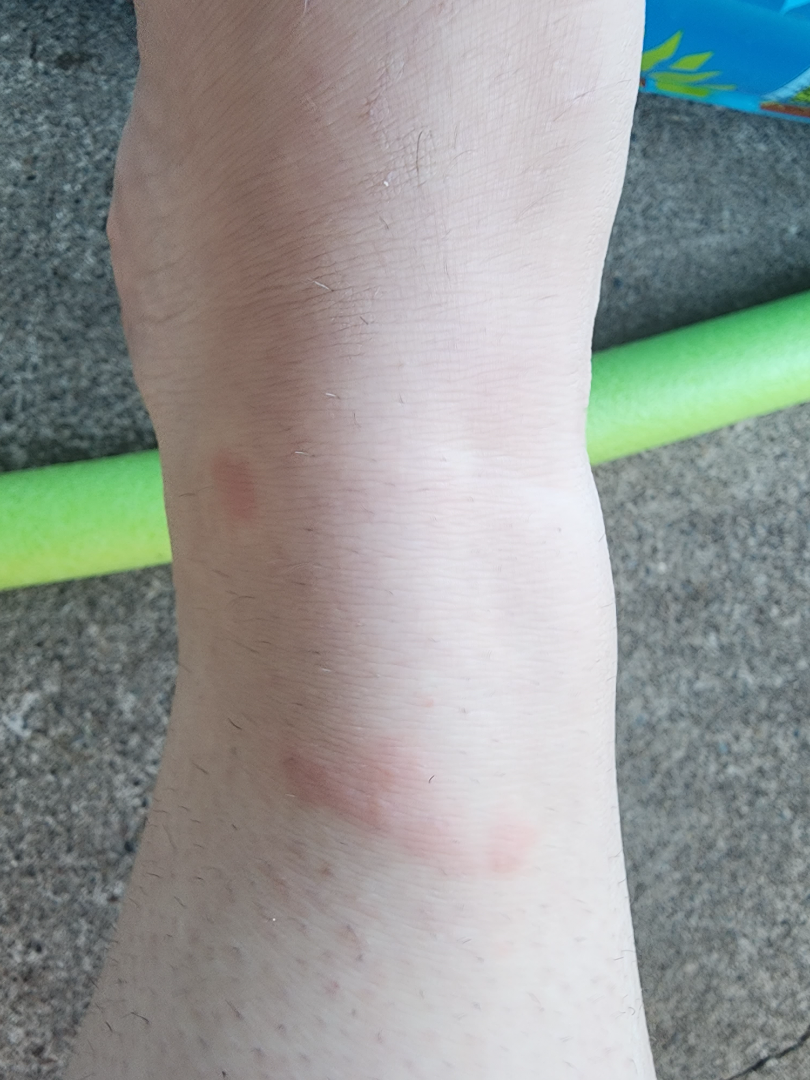Review: The reviewing dermatologist was unable to assign a differential diagnosis from the image. Patient information: Self-categorized by the patient as a rash. Reported duration is about one day. Located on the top or side of the foot. The contributor reports itching, pain and burning. Fitzpatrick II; lay reviewers estimated a MST of 1. A close-up photograph. The patient reported no systemic symptoms. The contributor reports the lesion is raised or bumpy.